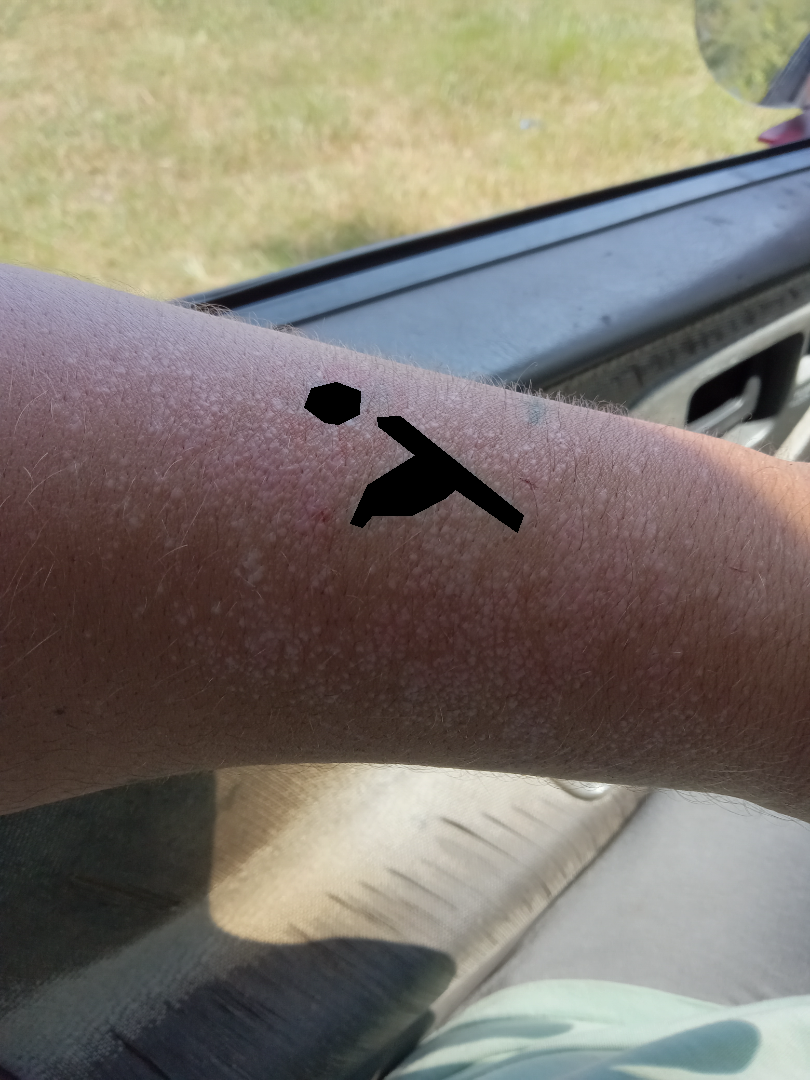{"body_site": "arm", "shot_type": "close-up", "differential": {"leading": ["Lichen planus/lichenoid eruption"]}}